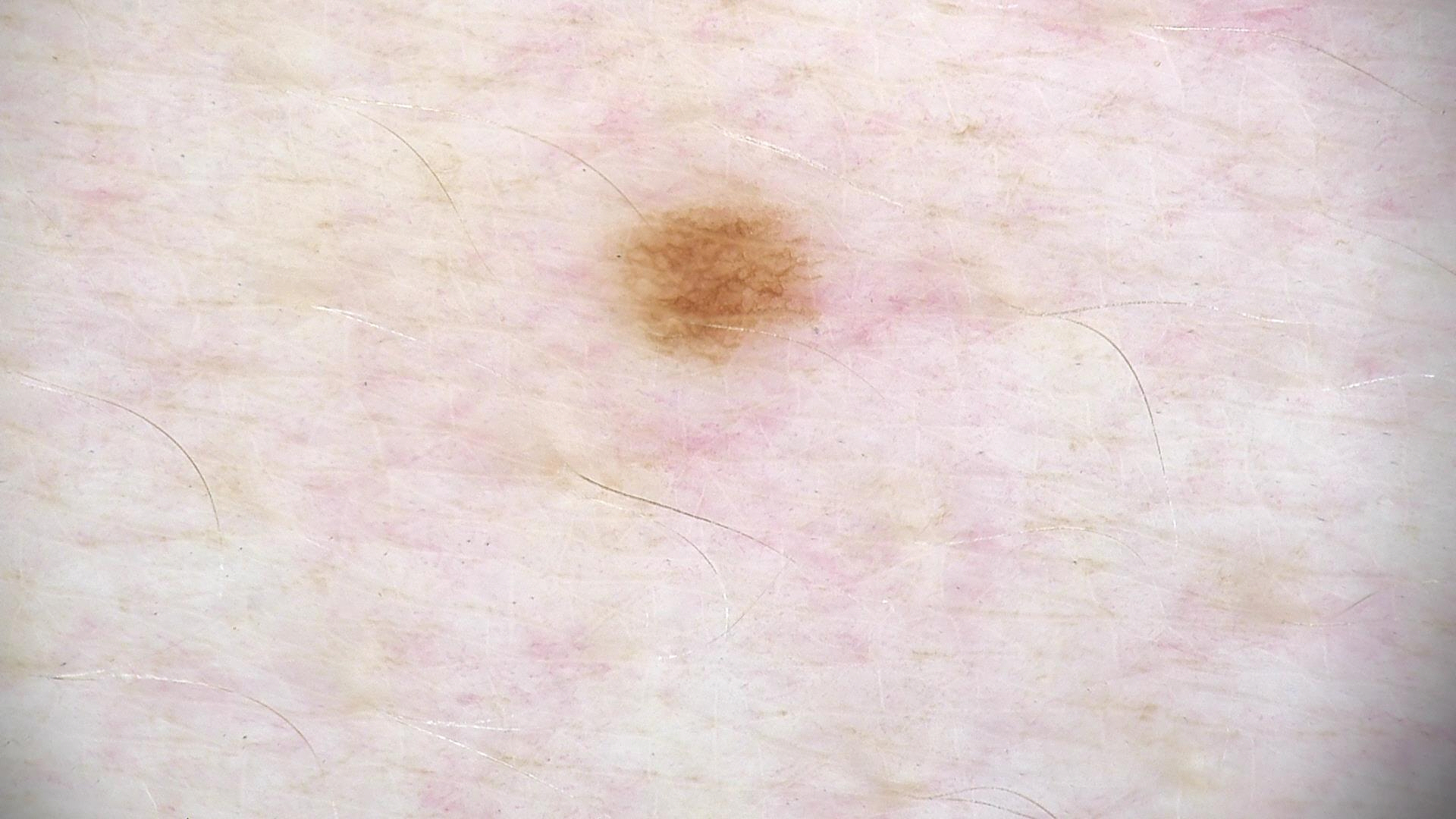Conclusion:
Consistent with a dysplastic junctional nevus.